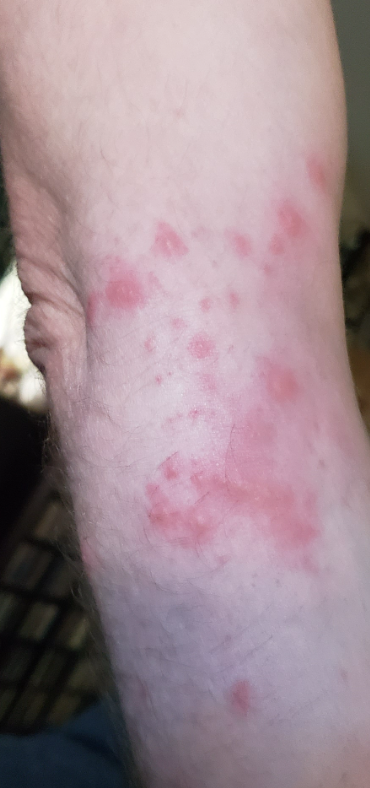differential — Impetigo (0.41); Folliculitis (0.41); Allergic Contact Dermatitis (0.18).